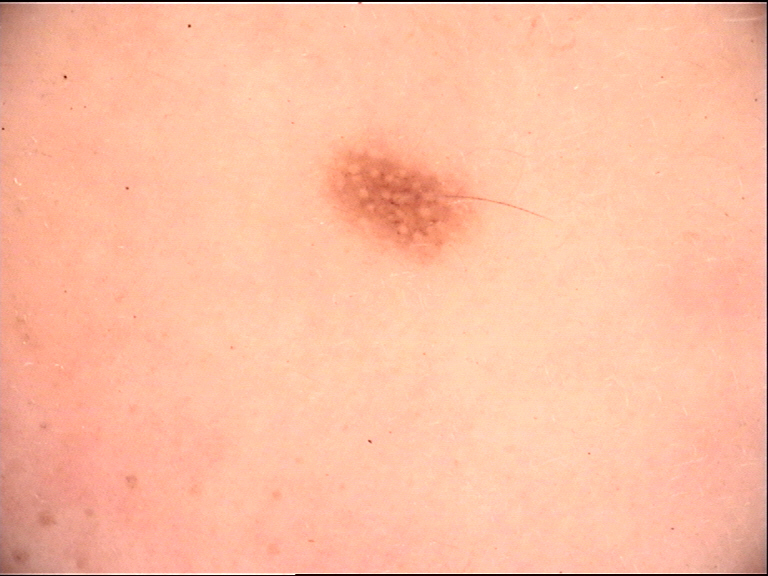Findings:
• modality — dermoscopy
• class — Miescher nevus (expert consensus)